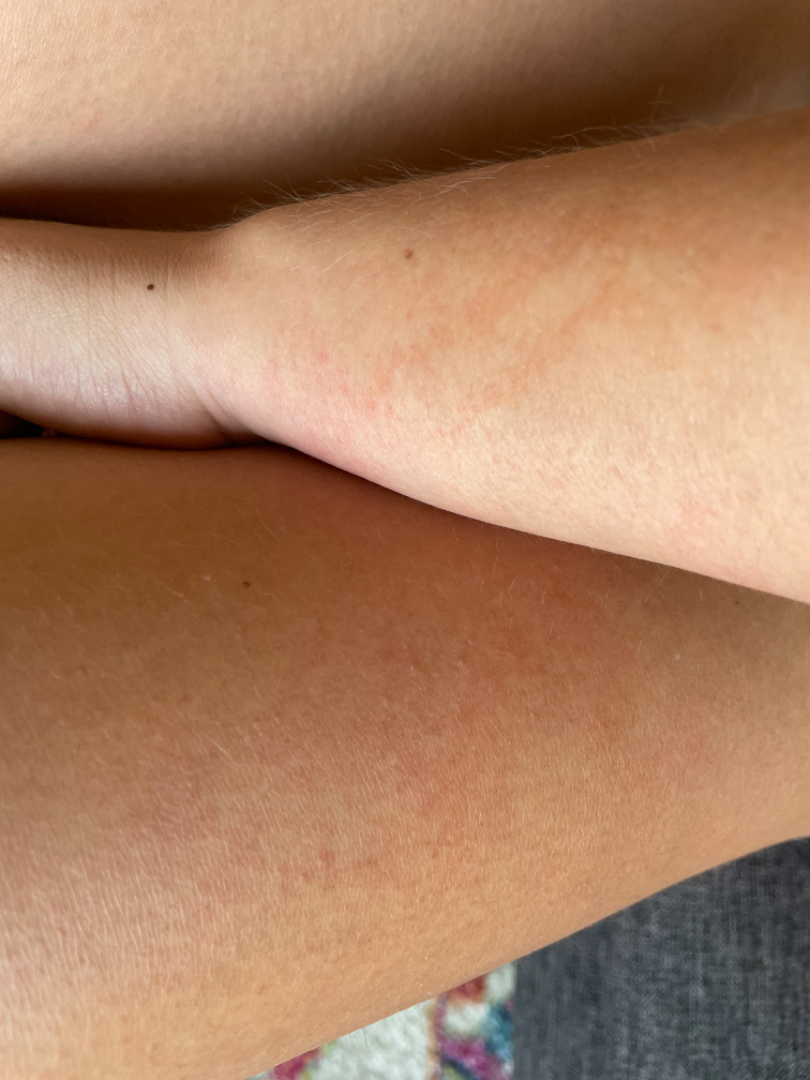Patient information:
The patient indicates itching. The affected area is the arm. The photograph was taken at an angle.
Review:
On photographic review, Drug Rash, Viral Exanthem and Sunburn were each considered, in no particular order.